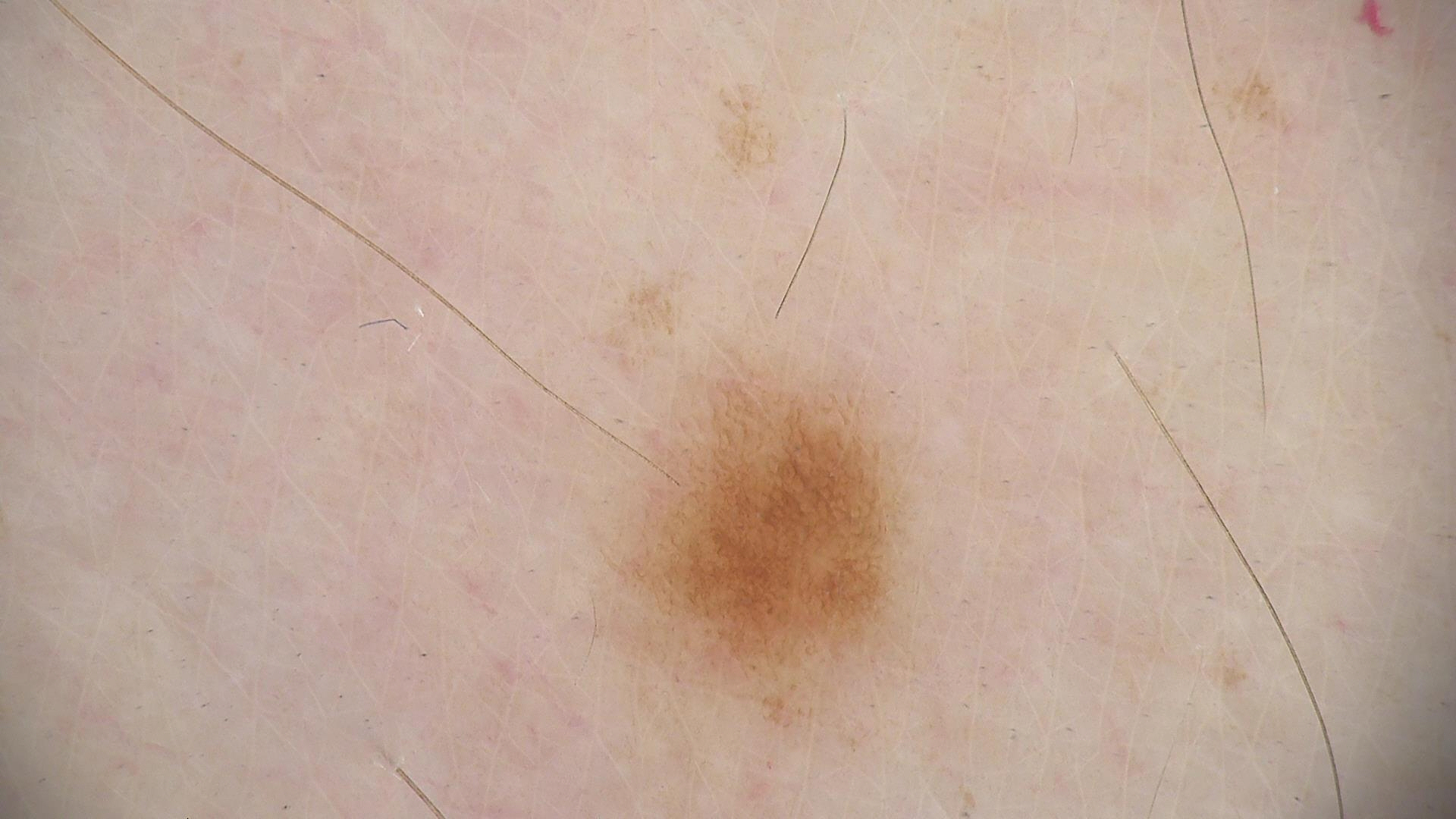Case:
– diagnosis — dysplastic junctional nevus (expert consensus)